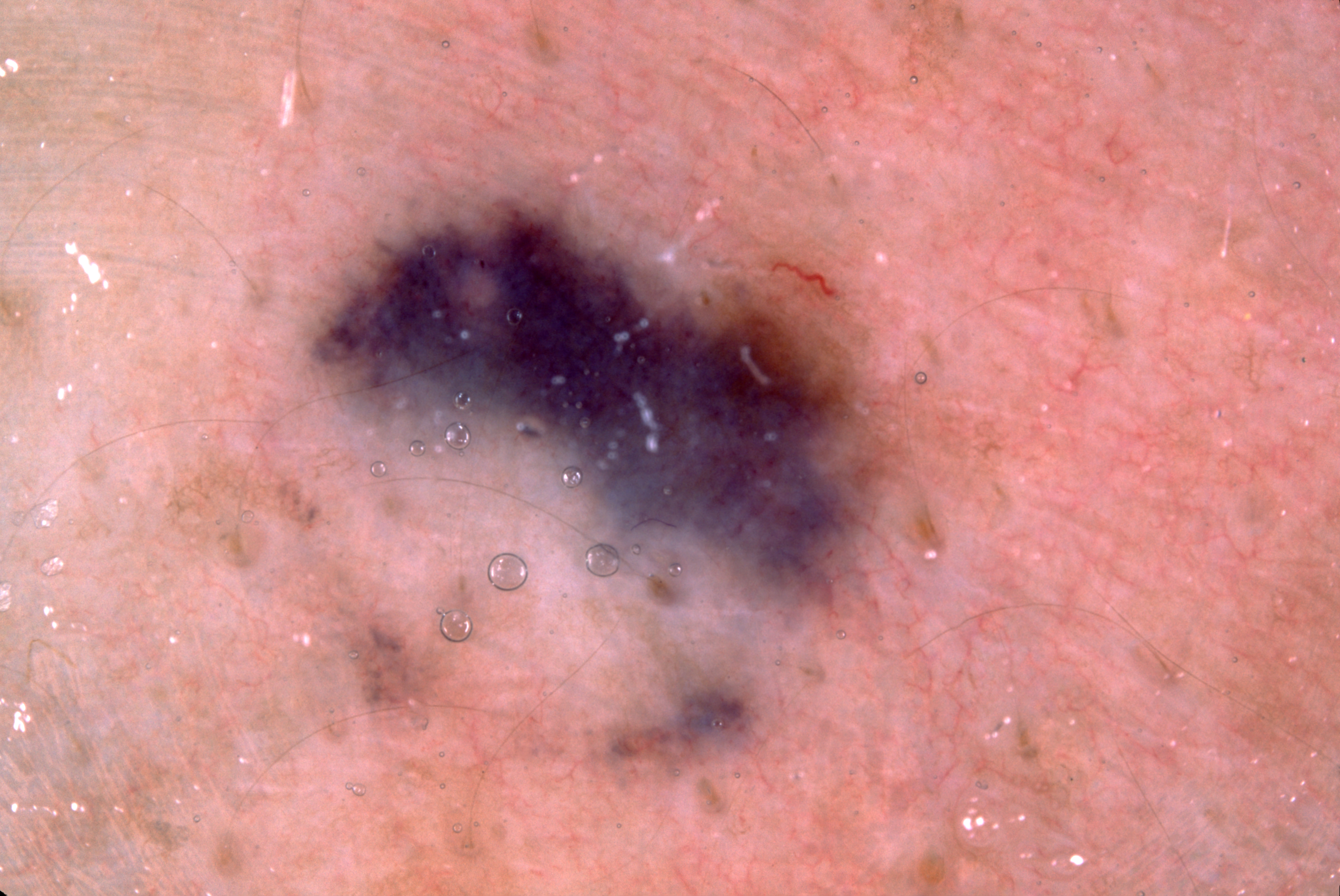A skin lesion imaged with a dermatoscope. As (left, top, right, bottom), lesion location: [187,126,960,810]. The lesion takes up about 35% of the image. Dermoscopically, the lesion shows pigment network, with no streaks, milia-like cysts, or negative network. The diagnostic assessment was a melanocytic nevus.